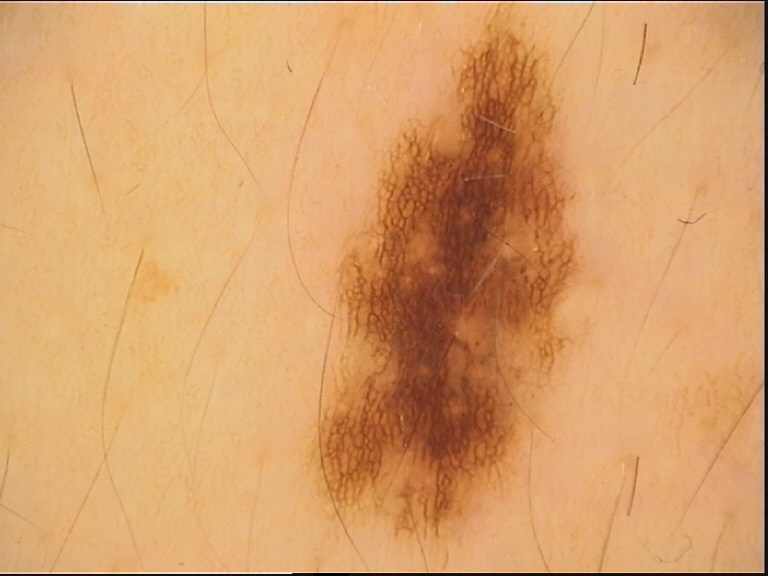{
  "image": "dermoscopy",
  "diagnosis": {
    "name": "dysplastic junctional nevus",
    "code": "jd",
    "malignancy": "benign",
    "super_class": "melanocytic",
    "confirmation": "expert consensus"
  }
}